The subject is 50–59, female. The photograph is a close-up of the affected area. The lesion involves the leg.
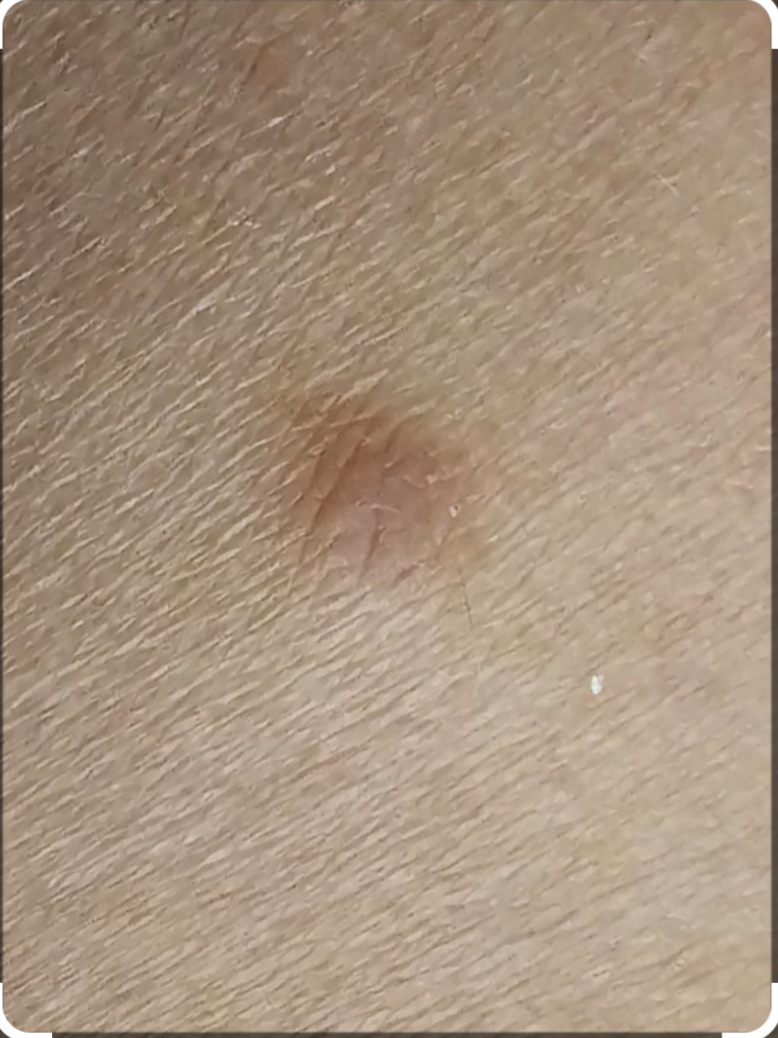differential diagnosis: the leading consideration is Dermatofibroma.